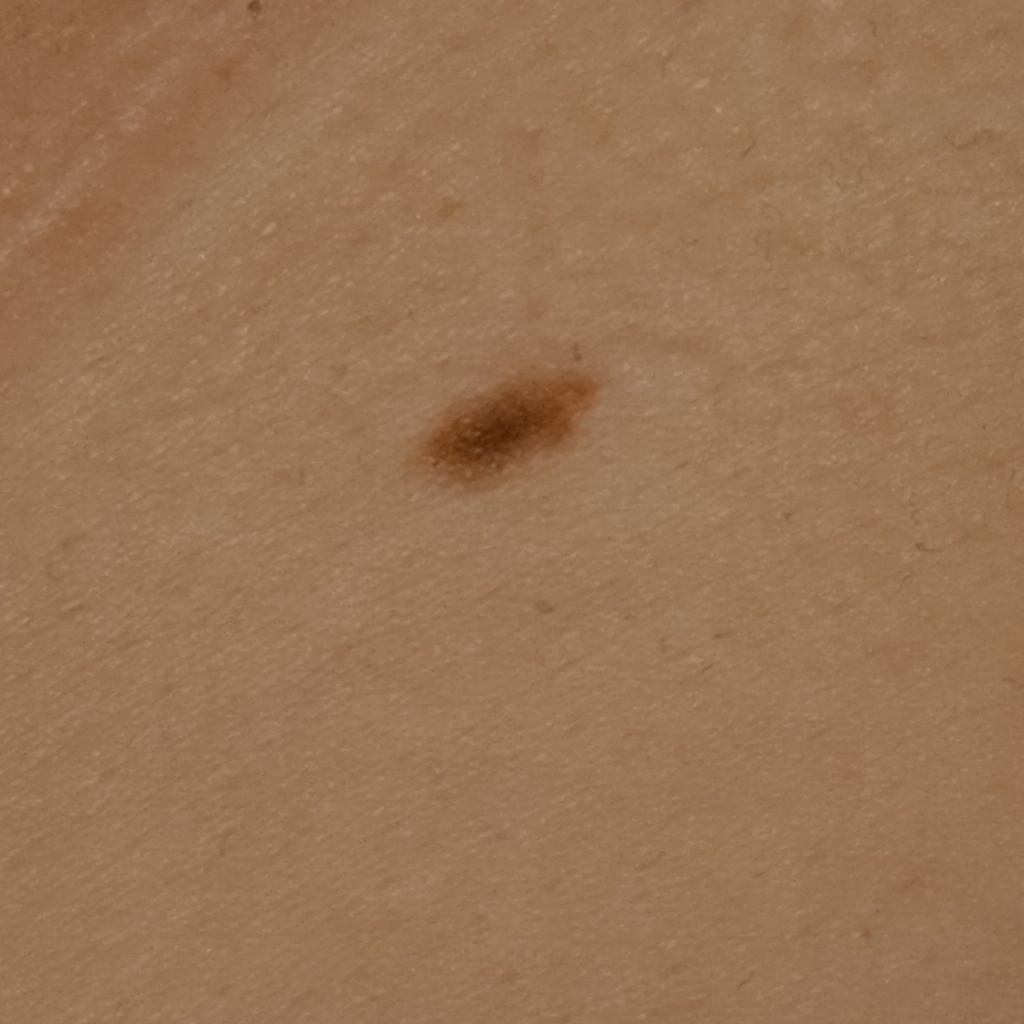Acquired for a research image collection, with no referral diagnosis. A clinical close-up of a skin lesion. A female subject 35 years old. The lesion involves the torso. Measuring roughly 6.3 mm. The diagnostic impression was a melanocytic nevus.